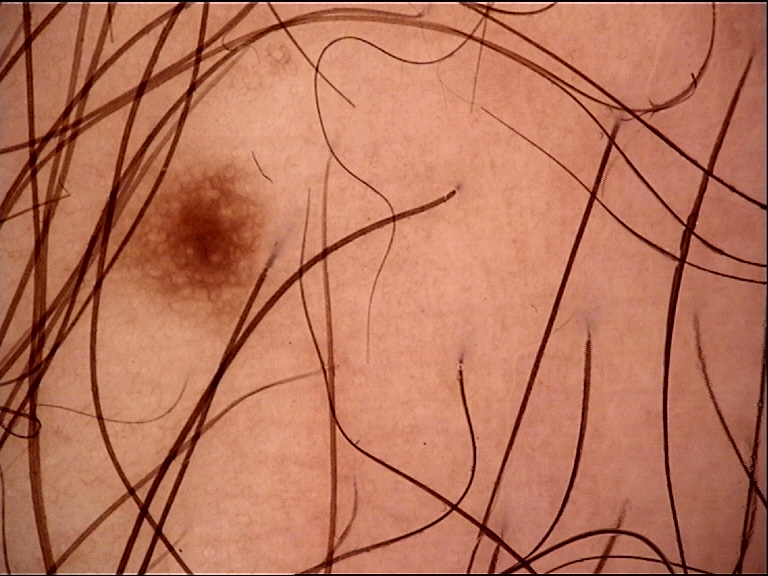Case:
A dermoscopic close-up of a skin lesion.
Impression:
The diagnosis was a banal lesion — a junctional nevus.